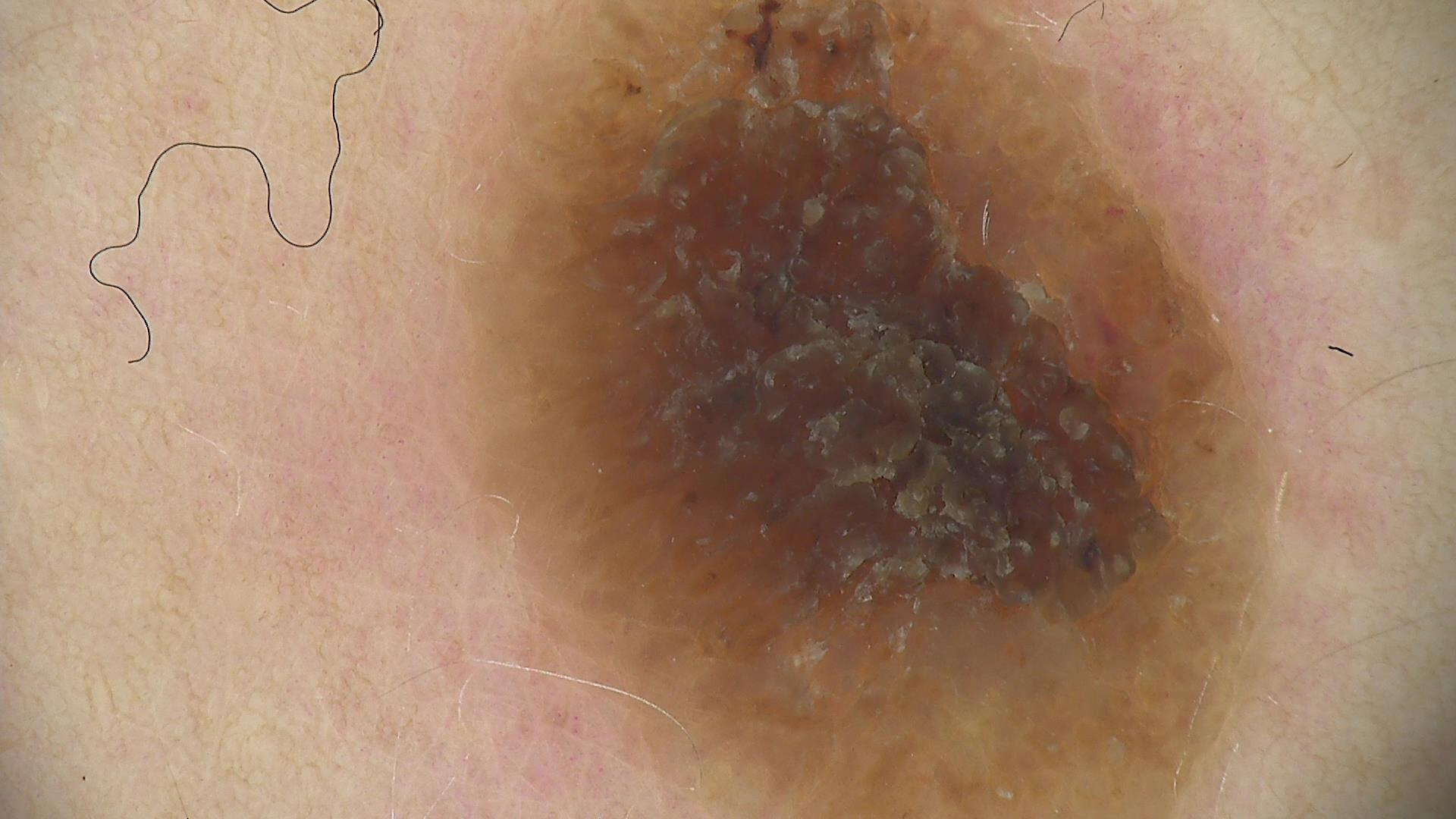Diagnosed as a seborrheic keratosis.